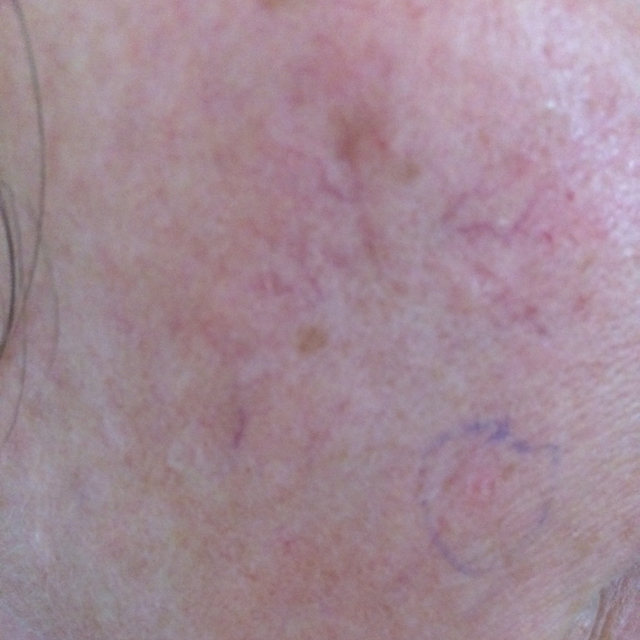A patient age 41. The patient describes that the lesion itches. Consistent with a lesion of indeterminate malignant potential — an actinic keratosis.